A male patient aged approximately 80; contact-polarized dermoscopy of a skin lesion:
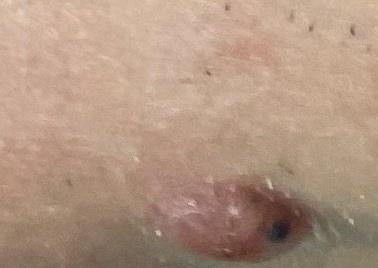Image and clinical context: Located on the head or neck. Diagnosis: Histopathologically confirmed as a basal cell carcinoma.